A female subject aged around 25. A skin lesion imaged with a dermatoscope:
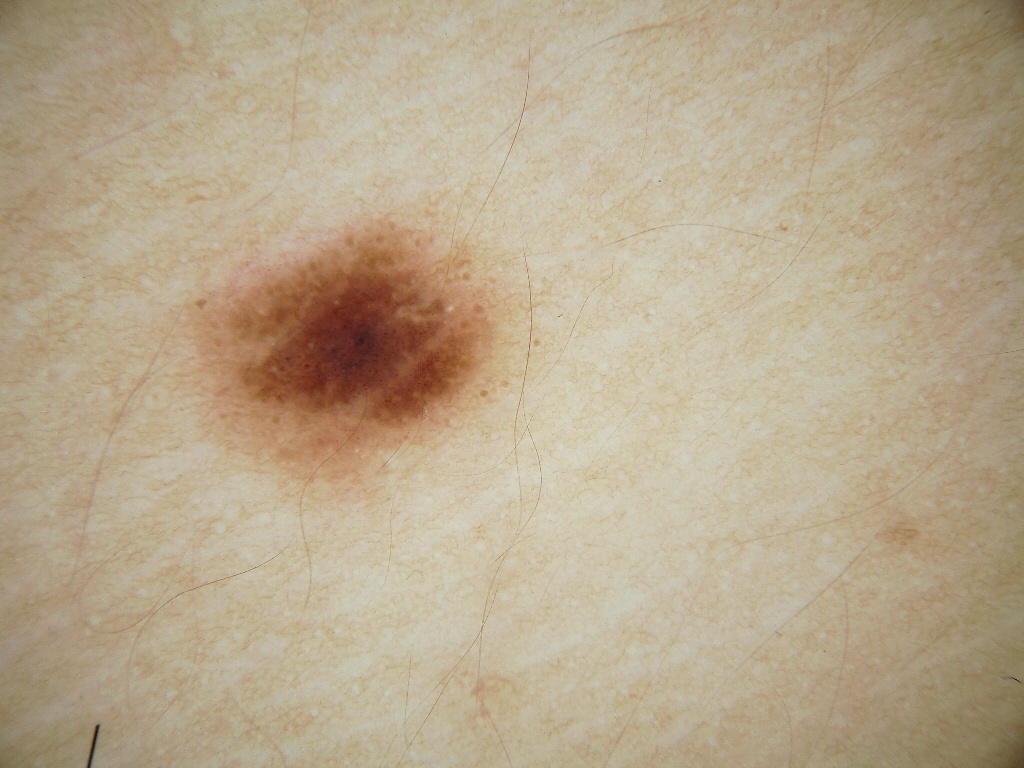Q: What does dermoscopy show?
A: globules and milia-like cysts; absent: negative network, streaks, and pigment network
Q: What is the lesion's bounding box?
A: [150, 187, 561, 503]
Q: What is this lesion?
A: a melanocytic nevus